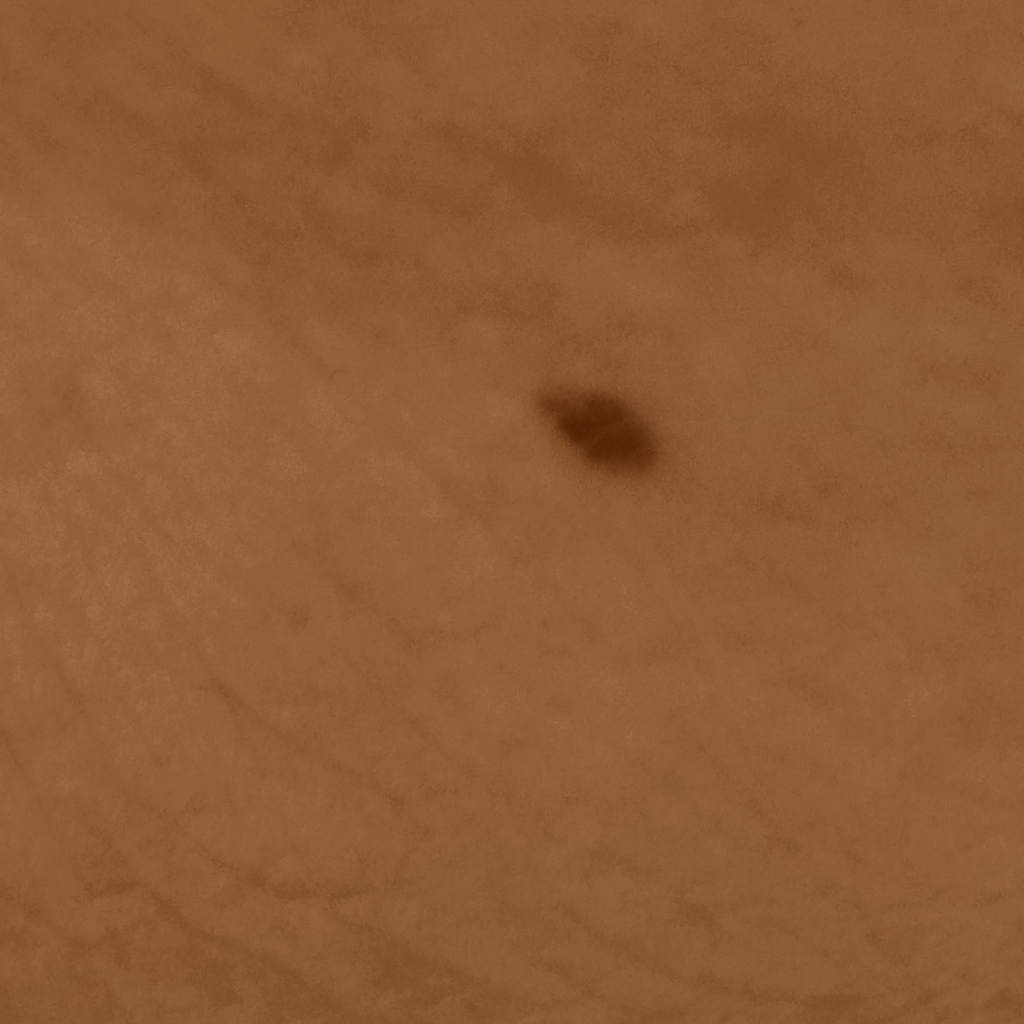Findings: A clinical photograph of a skin lesion. Acquired for a research image collection, with no referral diagnosis. A female patient 60 years of age. Conclusion: Dermatologist review favored a seborrheic keratosis.